A dermoscopy image of a single skin lesion:
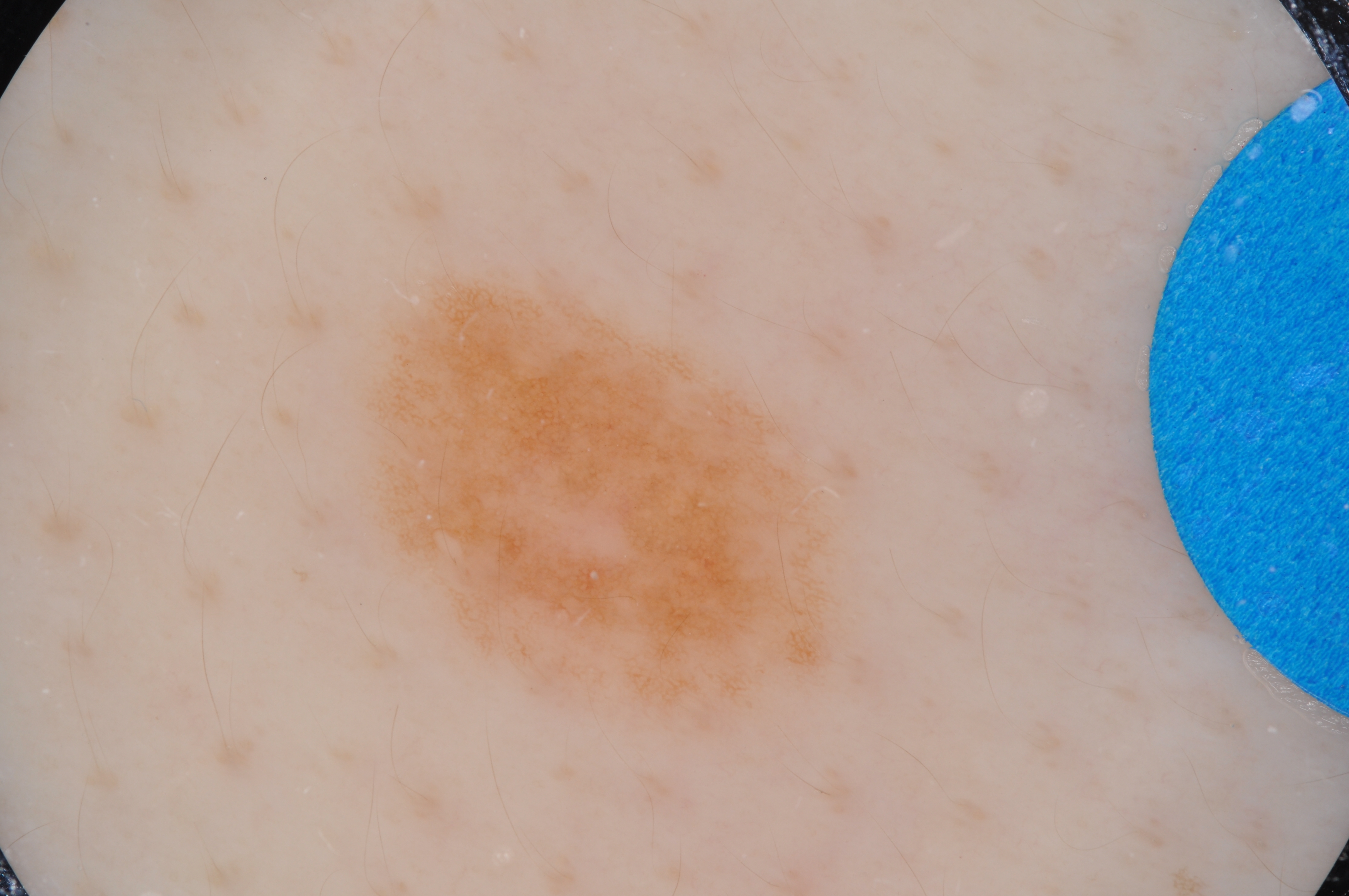Lesion location: x1=359, y1=270, x2=845, y2=733.
Diagnosed as a melanocytic nevus.